Dermoscopy of a skin lesion.
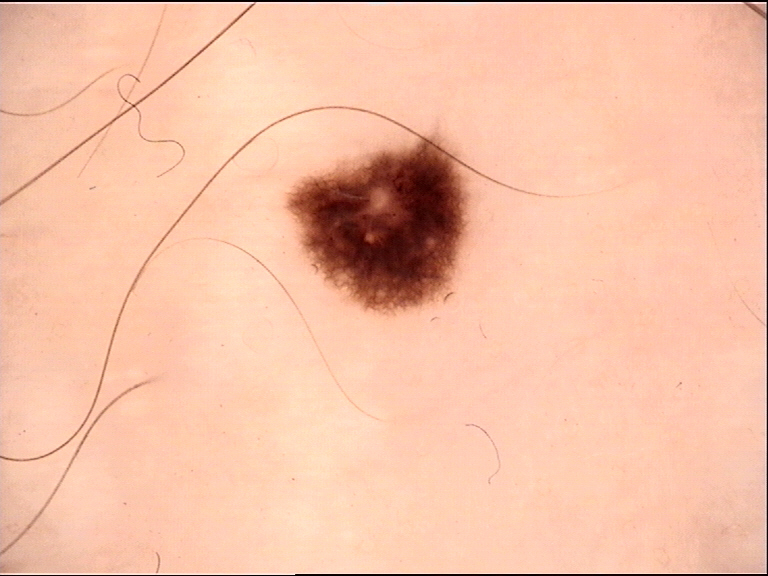diagnosis — dysplastic junctional nevus (expert consensus).